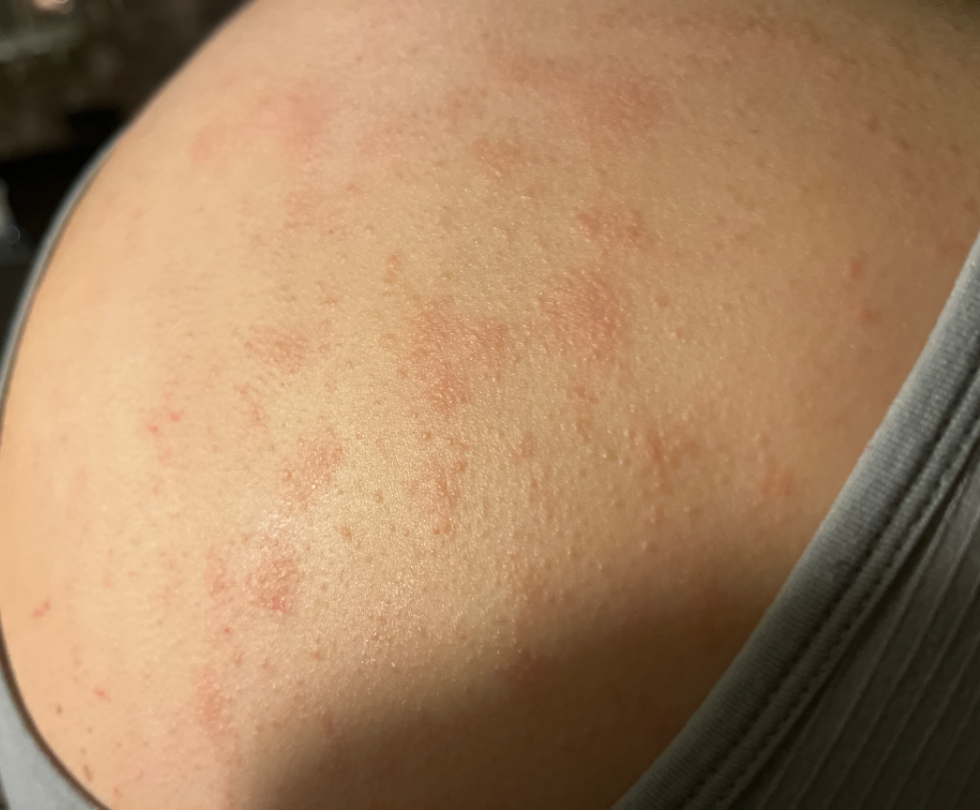History: The affected area is the front of the torso, back of the torso, head or neck and arm. The photograph was taken at an angle. Impression: One reviewing dermatologist: the favored diagnosis is Eczema; also consider Drug Rash; with consideration of Inflicted skin lesions.